The subject is a female aged approximately 75, a dermatoscopic image of a skin lesion.
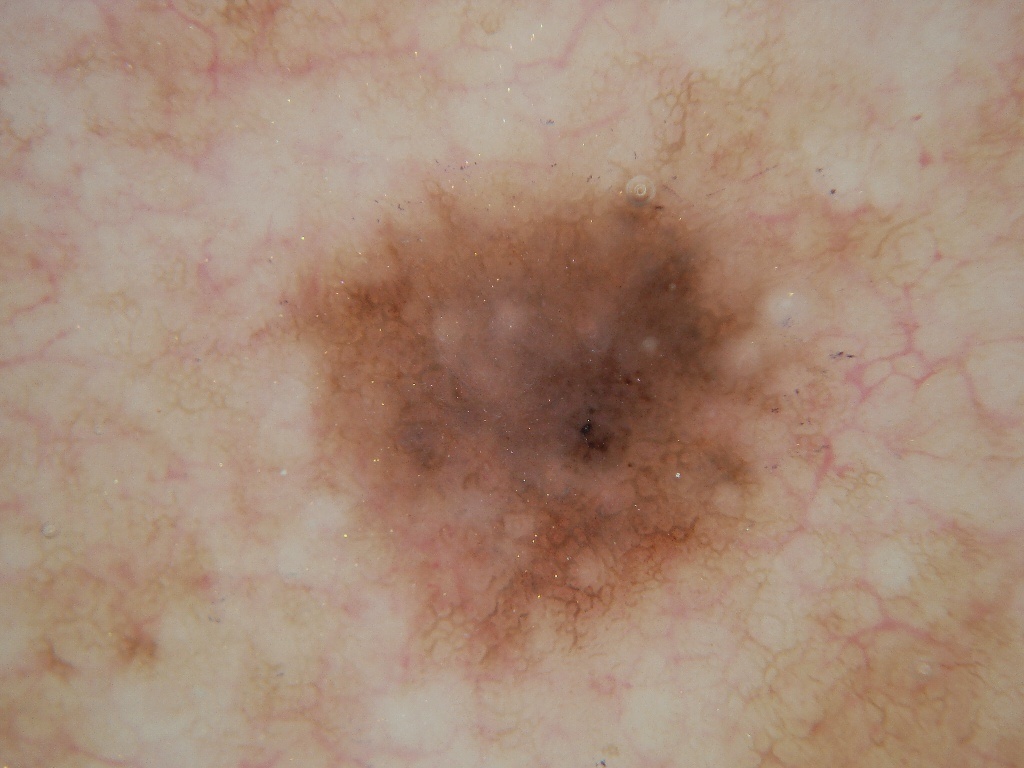lesion location = <box>240, 150, 845, 696</box> | lesion extent = ~32% of the field | features = pigment network; absent: streaks, globules, negative network, and milia-like cysts | assessment = a melanocytic nevus.